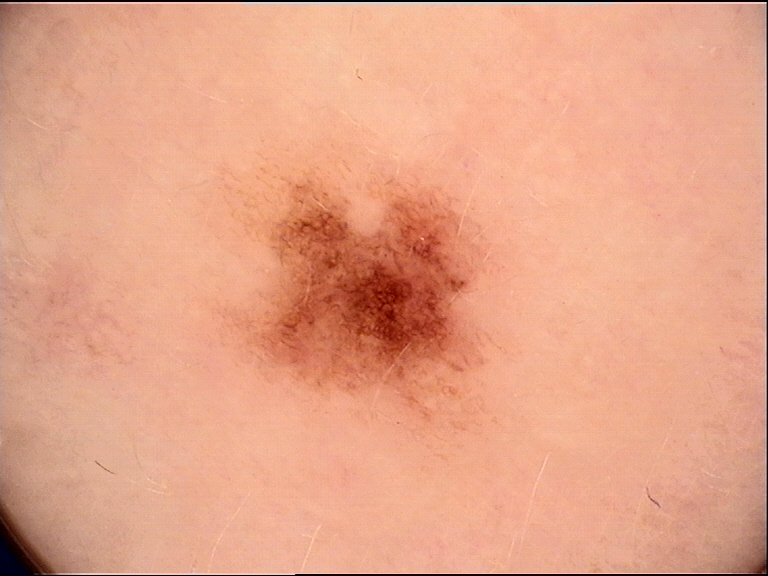Summary:
A dermoscopic close-up of a skin lesion.
Impression:
Labeled as a dysplastic junctional nevus.